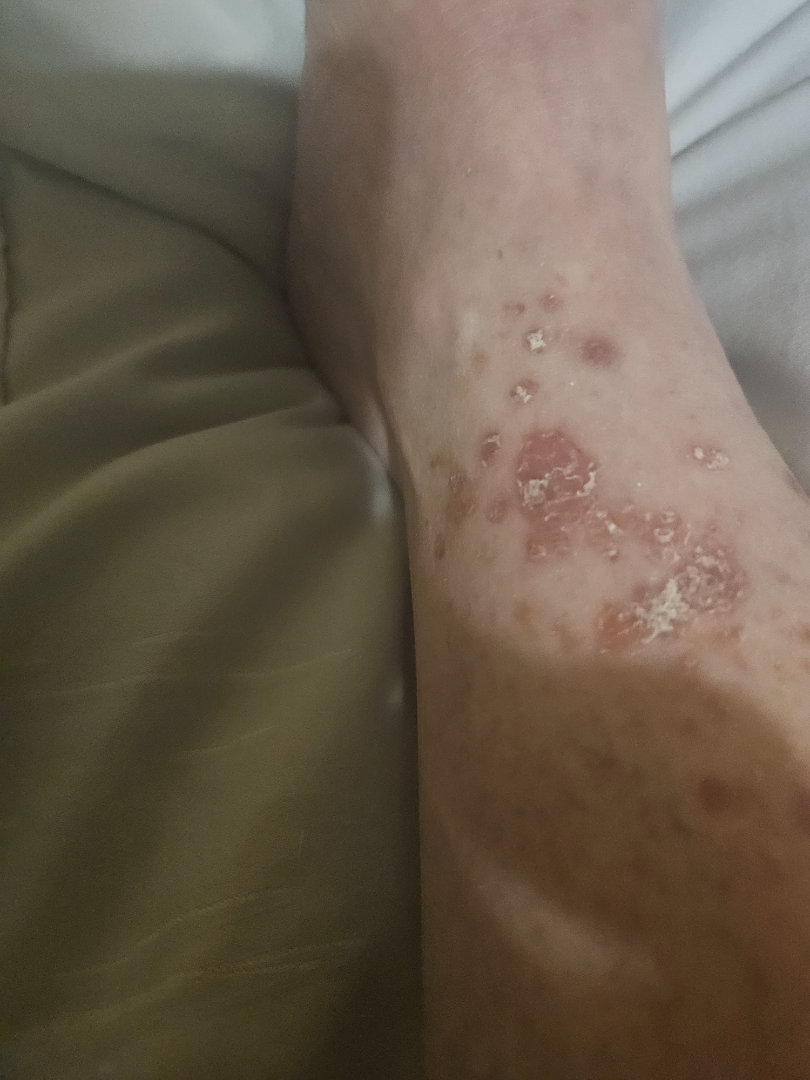Reviewed remotely by one dermatologist: consistent with Psoriasis.